A skin lesion imaged with a dermatoscope; a male patient in their 70s.
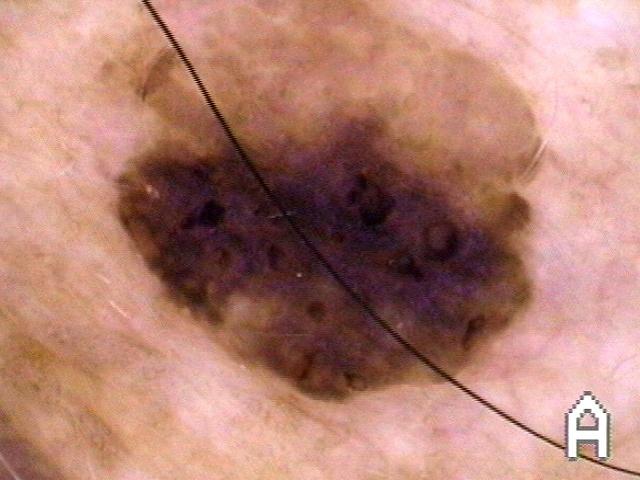{
  "lesion_location": {
    "region": "the trunk",
    "detail": "the anterior trunk"
  },
  "diagnosis": {
    "name": "Seborrheic keratosis",
    "malignancy": "benign",
    "confirmation": "expert clinical impression",
    "lineage": "epidermal"
  }
}